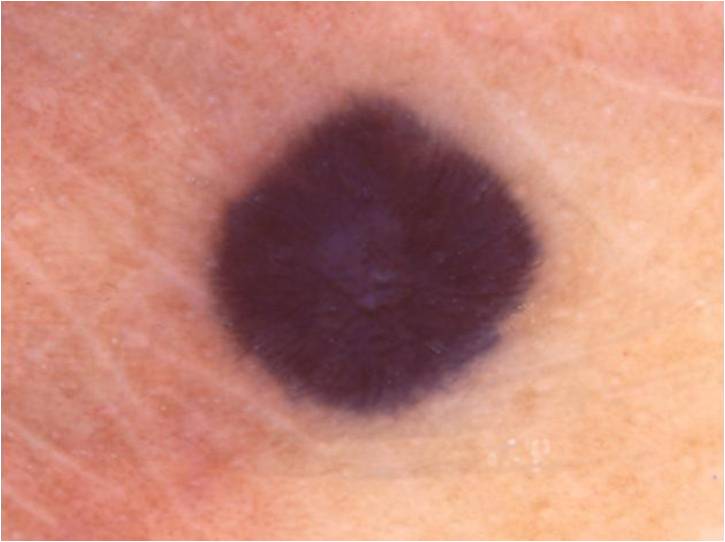Notes:
- subject — male, roughly 65 years of age
- modality — dermatoscopic image of a skin lesion
- bounding box — <box>204, 94, 539, 413</box>
- absent dermoscopic findings — streaks, globules, pigment network, milia-like cysts, and negative network
- assessment — a melanocytic nevus